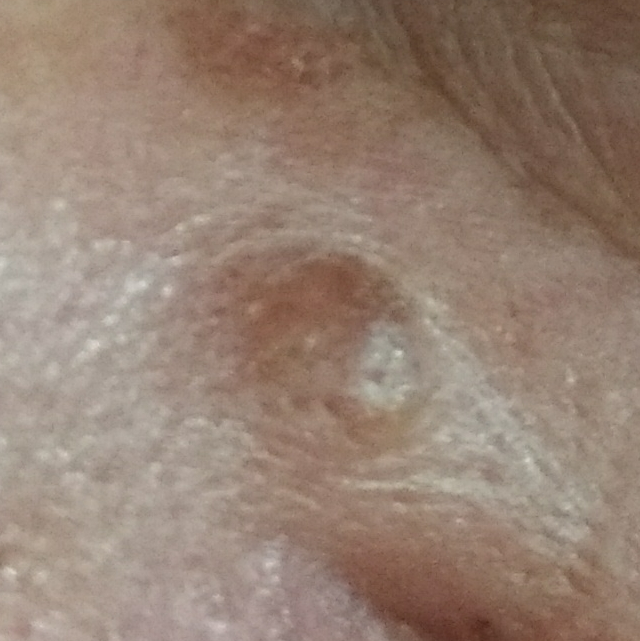Findings: A subject 56 years old. The lesion is on the face. The patient reports that the lesion is elevated, but has not bled. Conclusion: Clinically diagnosed as a nevus.